Male subject, age 18–29; the photograph was taken at a distance; no relevant lesion symptoms reported; texture is reported as fluid-filled and raised or bumpy; no constitutional symptoms were reported; reported duration is about one day; the arm is involved; self-categorized by the patient as acne.
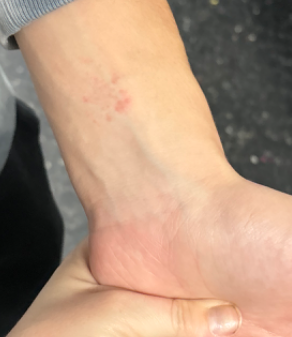Findings:
• differential diagnosis — Allergic Contact Dermatitis (weight 1.00)